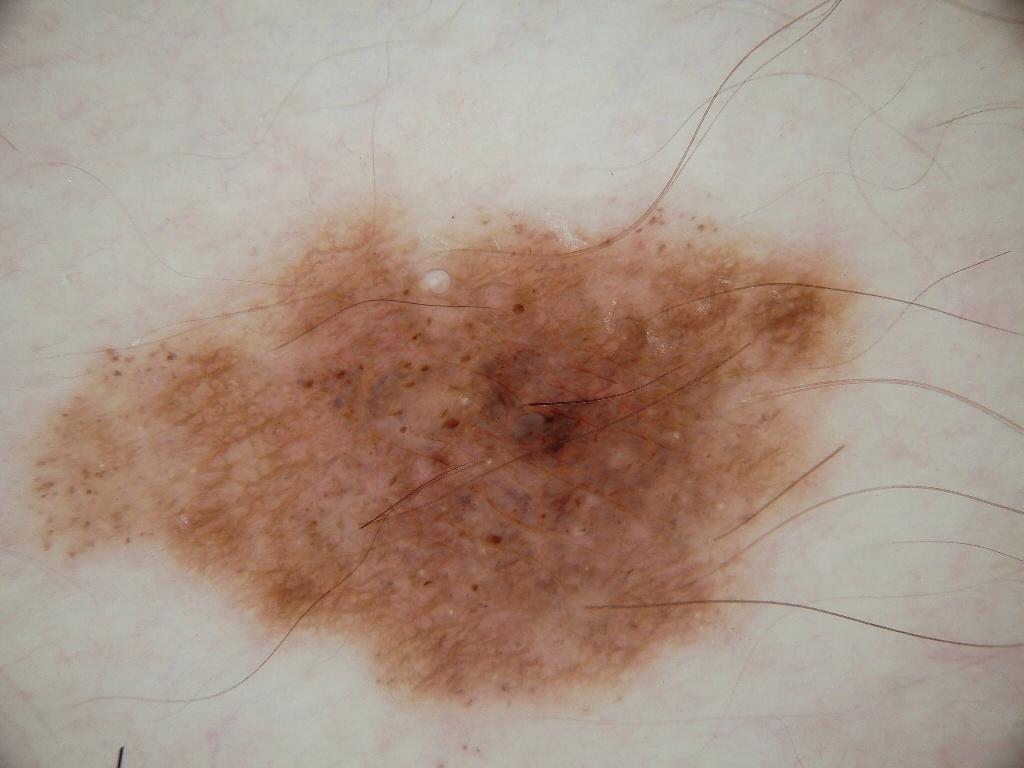imaging=dermoscopic image | subject=male, aged 18-22 | lesion location=[20,206,858,708] | dermoscopic findings=globules, milia-like cysts, and pigment network; absent: negative network and streaks | diagnostic label=a melanocytic nevus.